Imaged for a research study, with no referral diagnosis recorded. The patient says their skin reddens with sun exposure. On a questionnaire the patient reported a history of sunbed use. A female subject 26 years old. A clinical photograph showing a skin lesion. The patient describes having numerous moles.
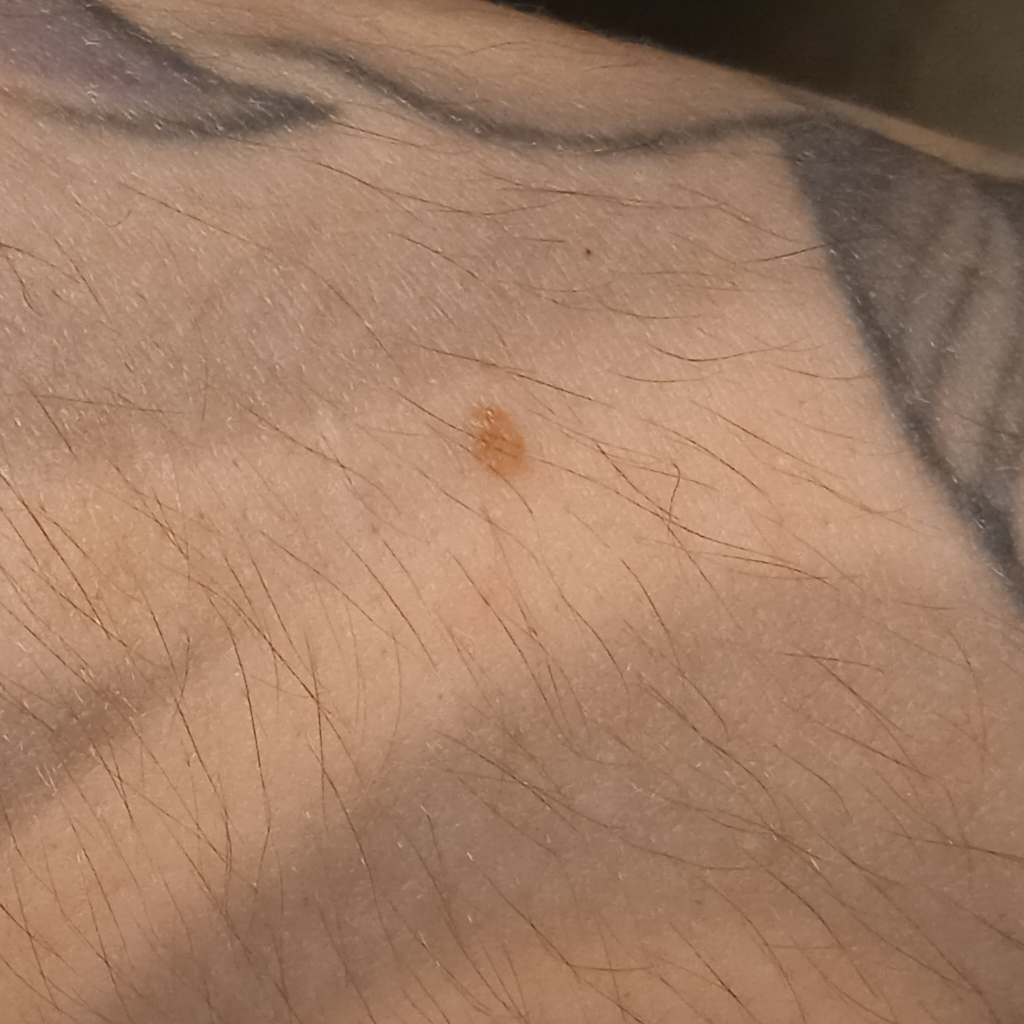  lesion_location: an arm
  lesion_size:
    diameter_mm: 3.4
  diagnosis:
    name: melanocytic nevus
    malignancy: benign